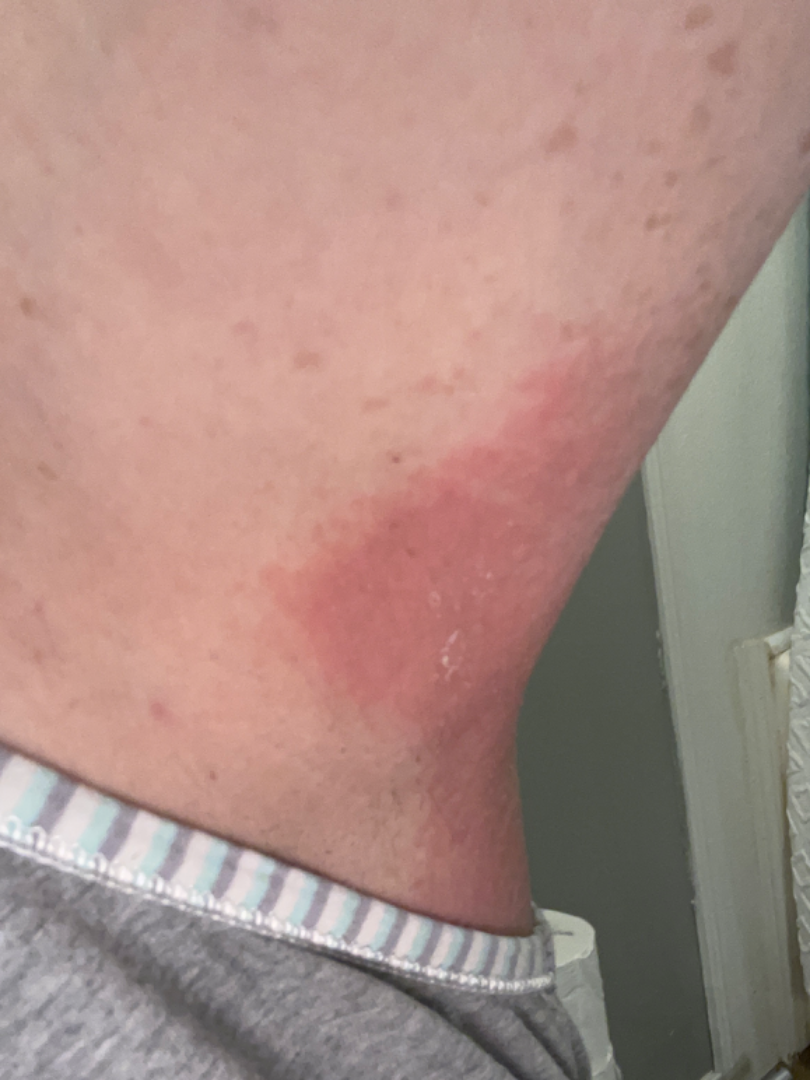History:
The patient is a female aged 50–59. The lesion involves the arm and head or neck. An image taken at an angle. The condition has been present for less than one week. Reported lesion symptoms include pain, itching and burning. Associated systemic symptoms include joint pain, shortness of breath, chills and fever. Self-categorized by the patient as a rash.
Impression:
Most consistent with Cellulitis; with consideration of Urticaria; also on the differential is Inflammatory dermatosis.